This image was taken at an angle; the arm, leg and back of the torso are involved:
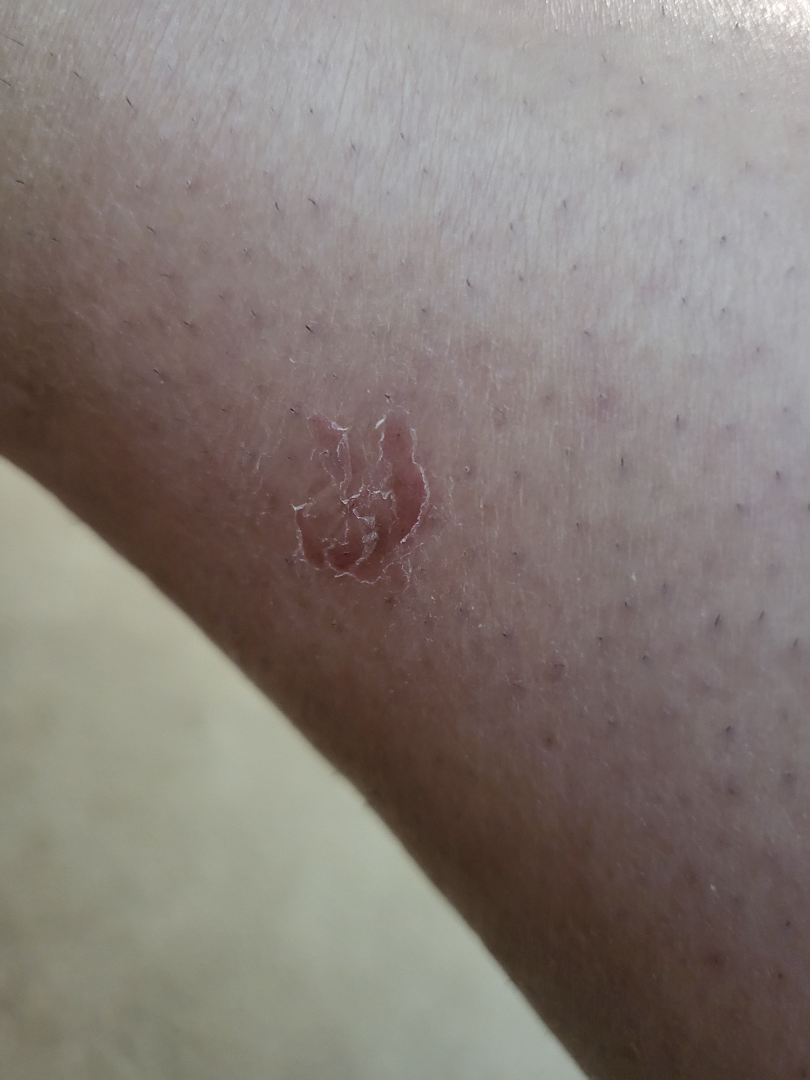The case was difficult to assess from the available photograph. Symptoms reported: itching. Texture is reported as rough or flaky.